Reported duration is one to four weeks; close-up view; located on the front of the torso, arm, back of the torso and head or neck; the lesion is described as raised or bumpy: 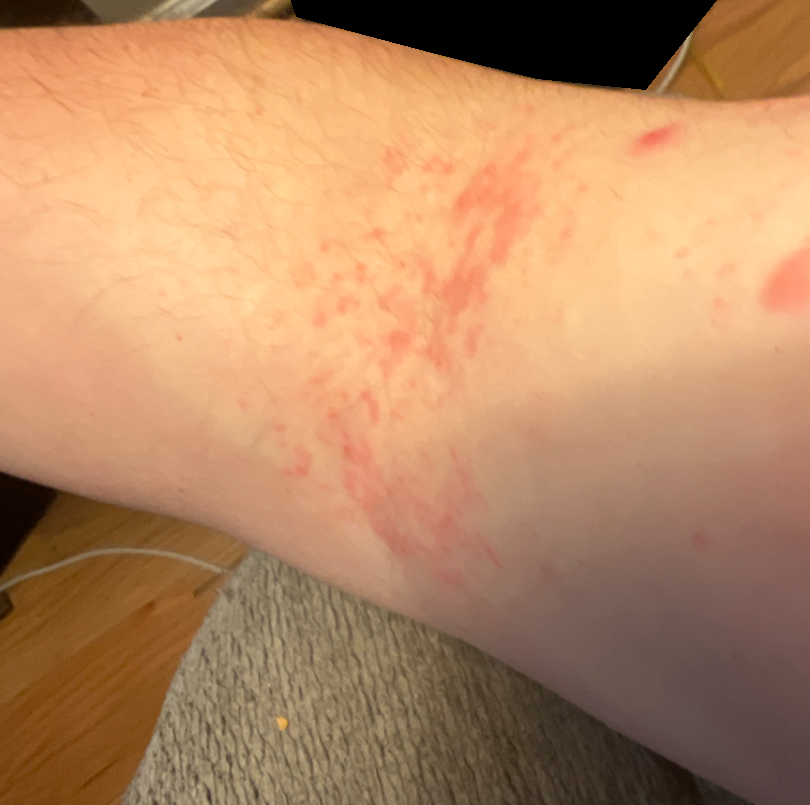Findings:
• dermatologist impression — one reviewing dermatologist: most consistent with Eczema